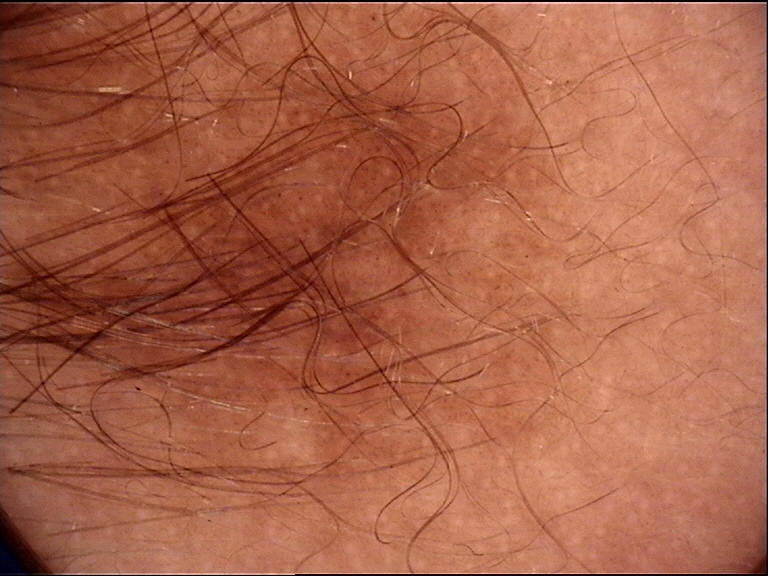This is a banal lesion. Consistent with a congenital junctional nevus.